A skin lesion imaged with a dermatoscope: 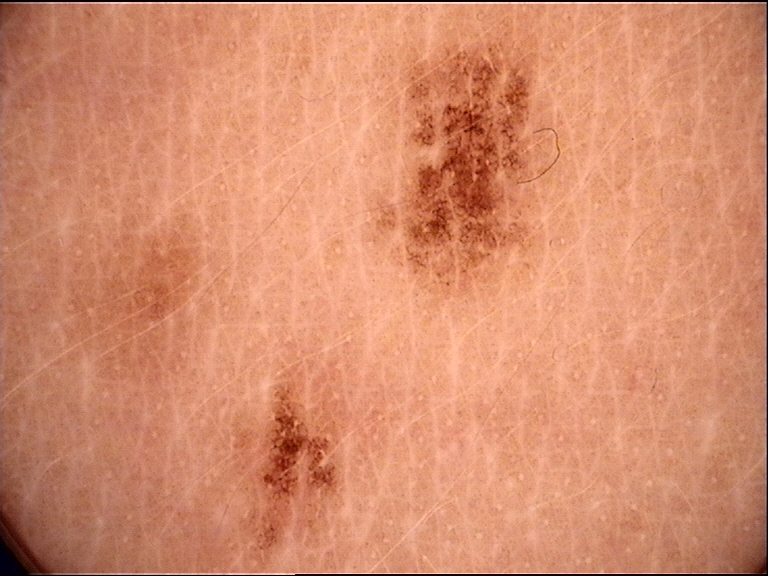Diagnosed as a banal lesion — a junctional nevus.